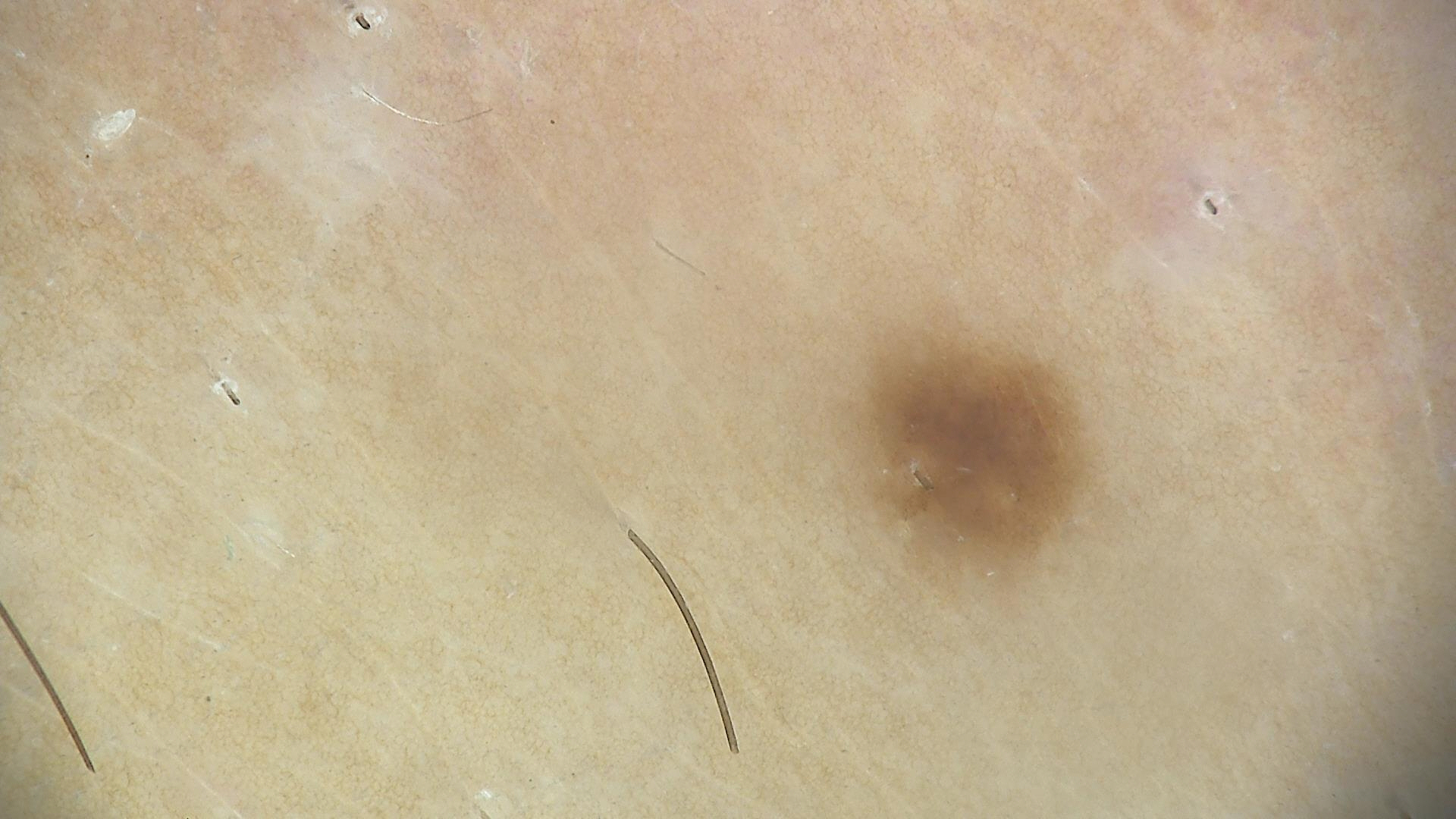Findings:
– label — dysplastic junctional nevus (expert consensus)